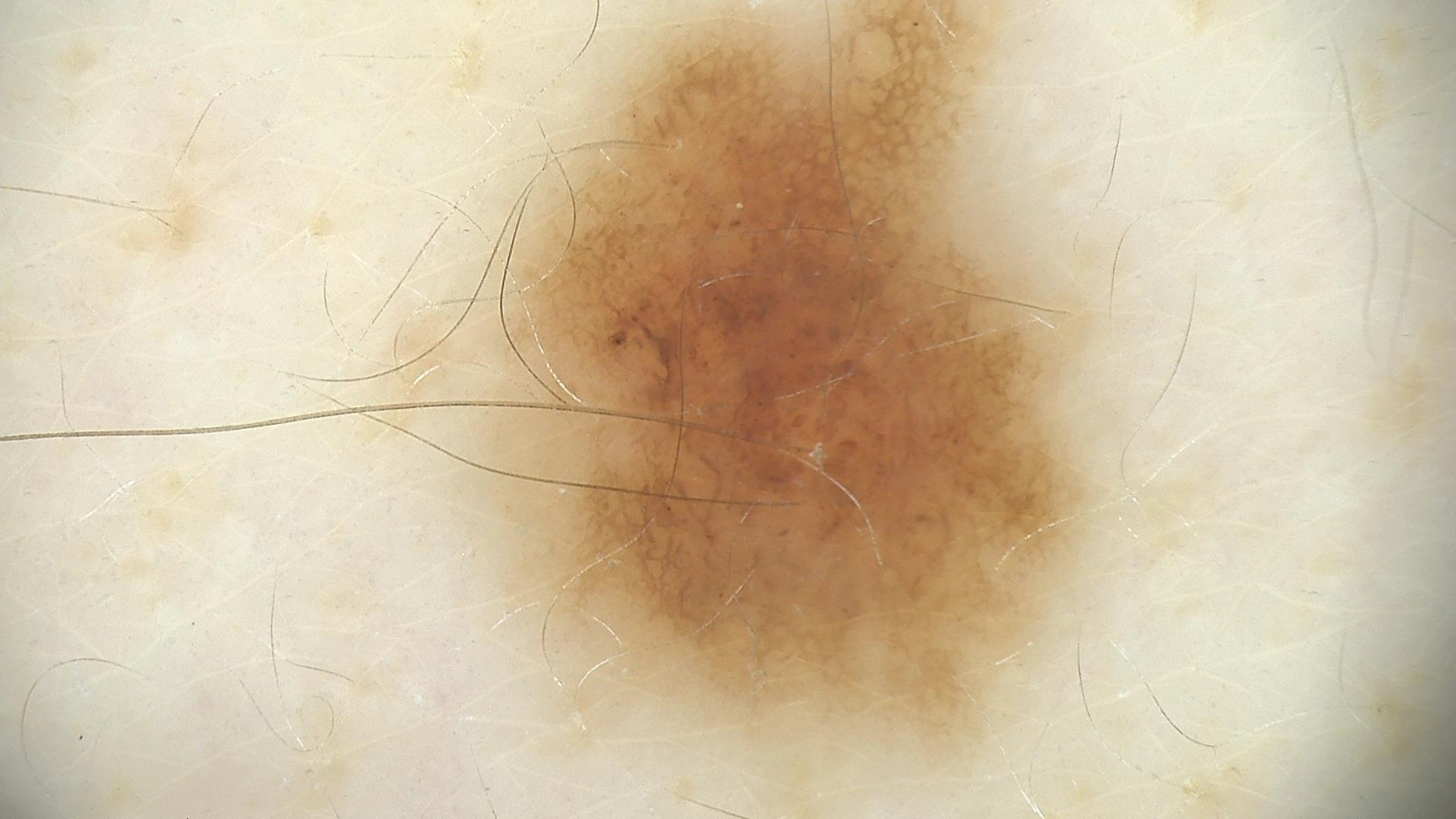Q: What is this lesion?
A: dysplastic junctional nevus (expert consensus)